A clinical photograph showing a skin lesion:
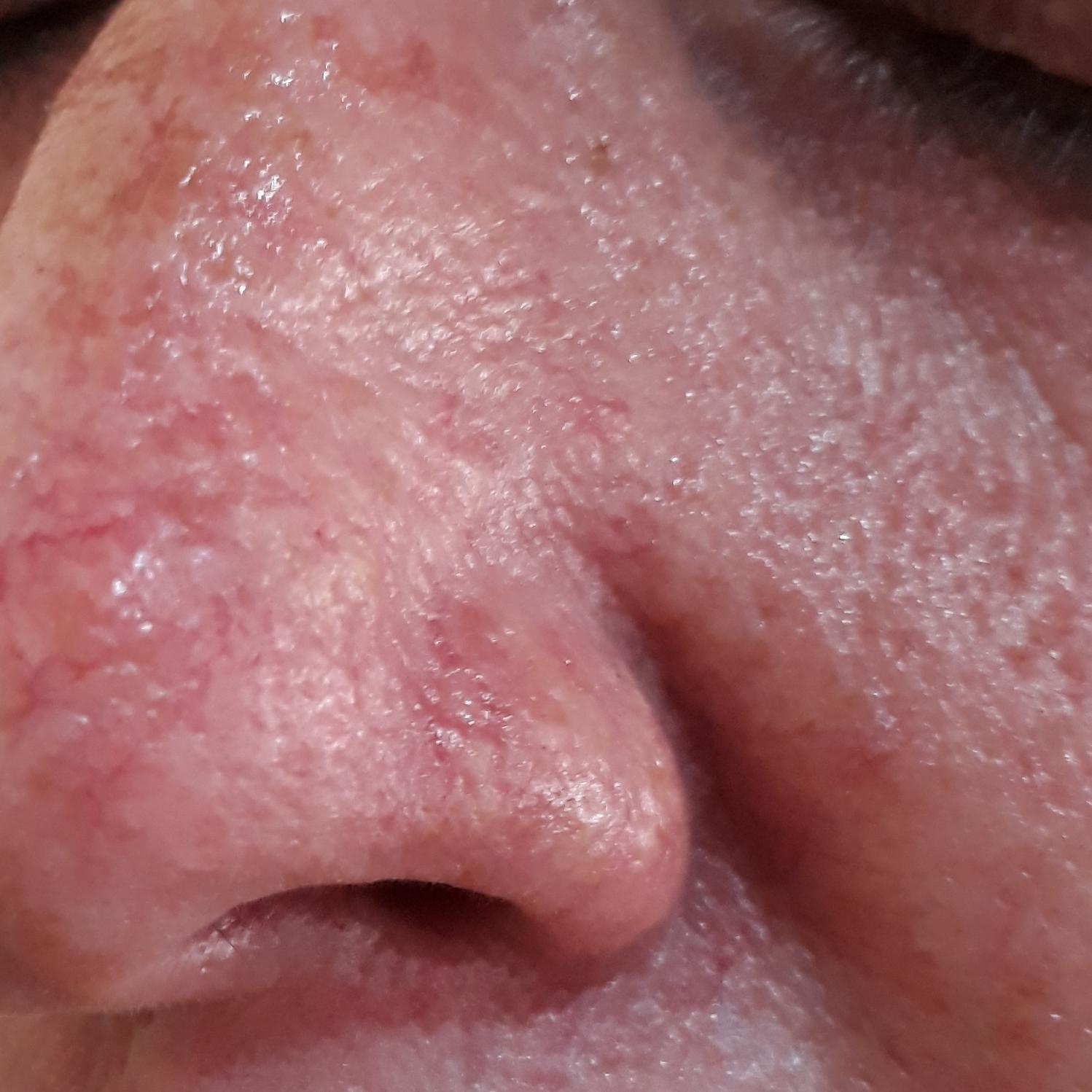Findings:
- diagnosis — actinic keratosis (clinical consensus)